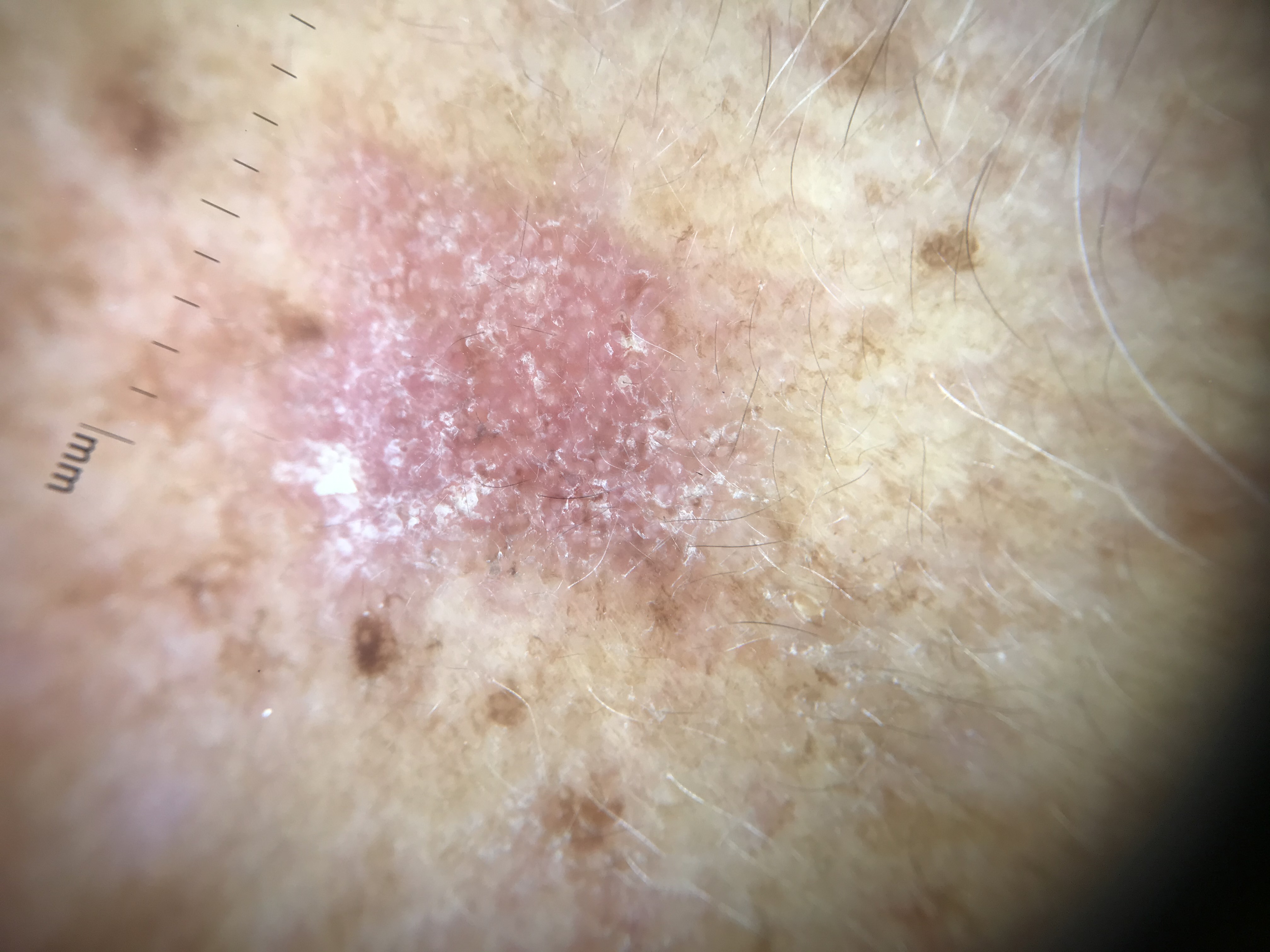Conclusion: The diagnostic label was an indeterminate, keratinocytic lesion — an actinic keratosis.